A dermoscopic photograph of a skin lesion.
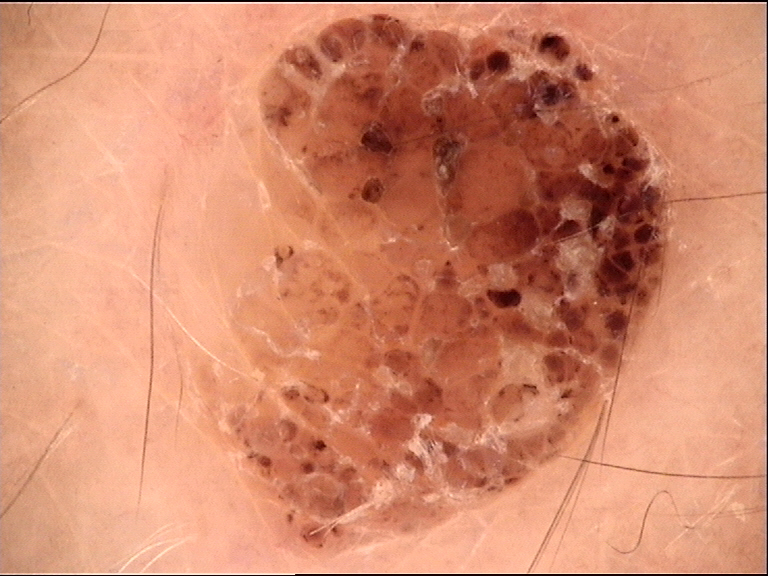The diagnosis was a compound nevus.